The subject is 18–29, female · the front of the torso and arm are involved · this image was taken at a distance:
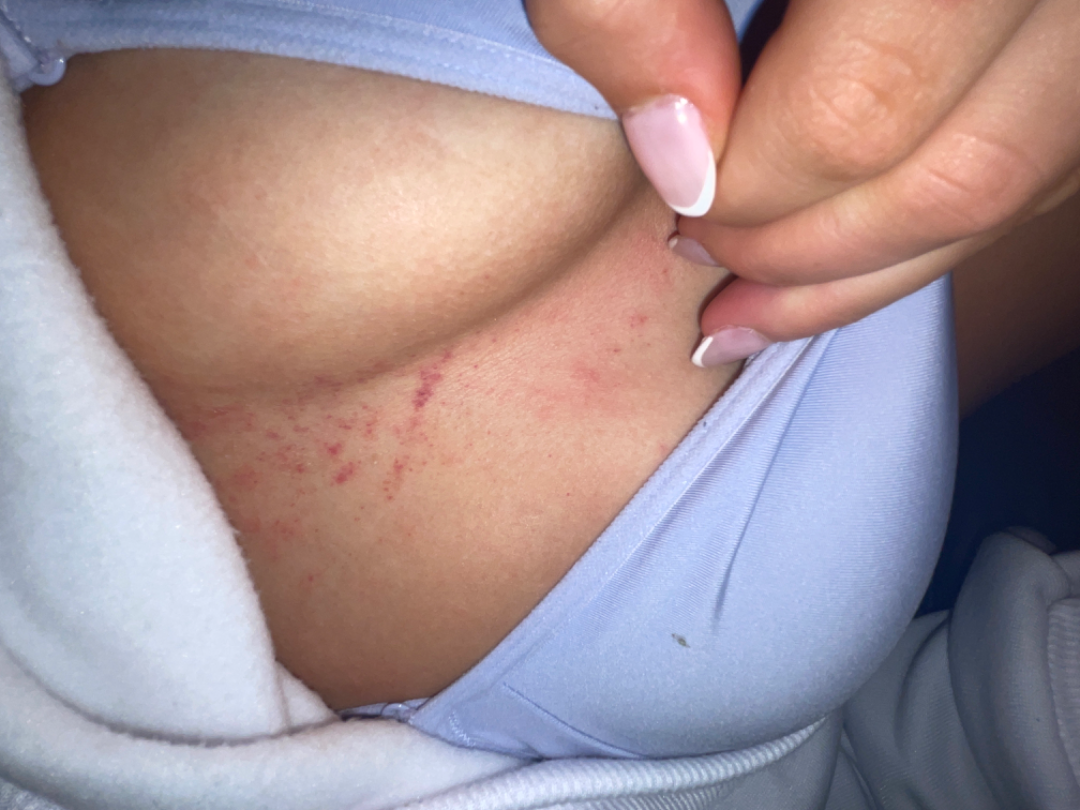Review: On remote dermatologist review, favoring Eczema; a more distant consideration is Traumatic petechiae; lower on the differential is Allergic Contact Dermatitis; less likely is Viral Exanthem; less probable is Leukocytoclastic Vasculitis.